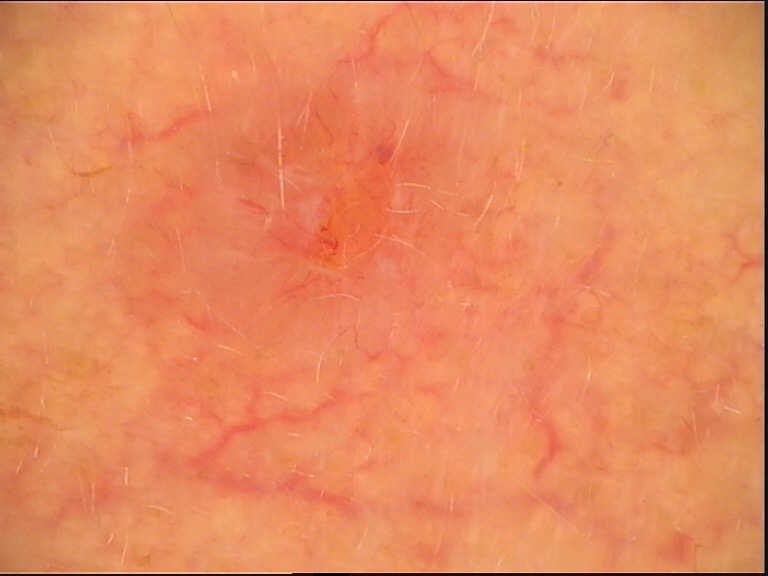- imaging · dermoscopy
- diagnostic label · basal cell carcinoma (biopsy-proven)